The chart documents a prior melanoma; Fitzpatrick skin type II:
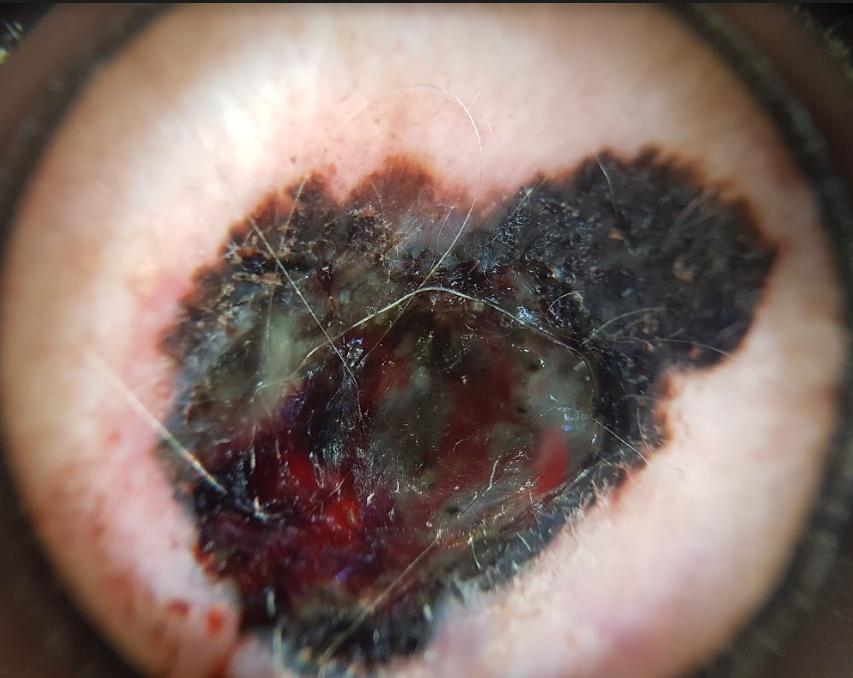| key | value |
|---|---|
| anatomic site | the head or neck |
| pathology | Melanoma (biopsy-proven) |